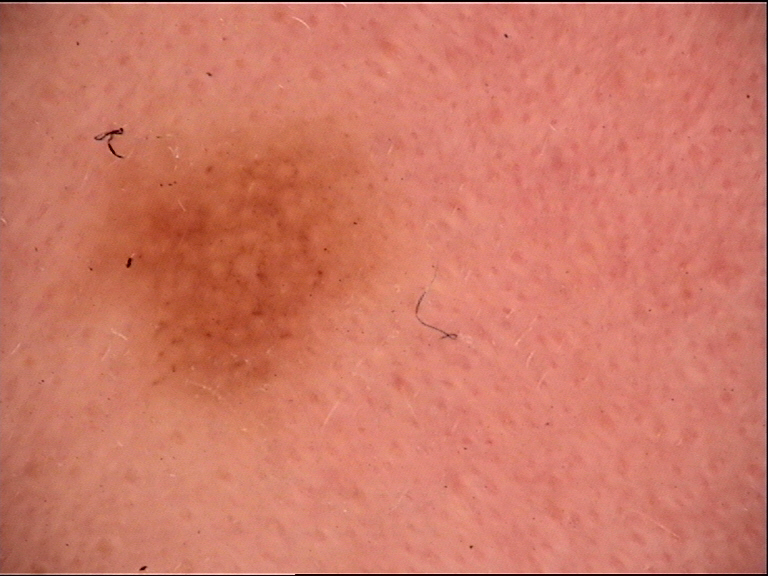A skin lesion imaged with a dermatoscope.
The diagnosis was a compound lesion — a Miescher nevus.